The lesion involves the arm · the photograph is a close-up of the affected area · the subject is a female aged 30–39 — 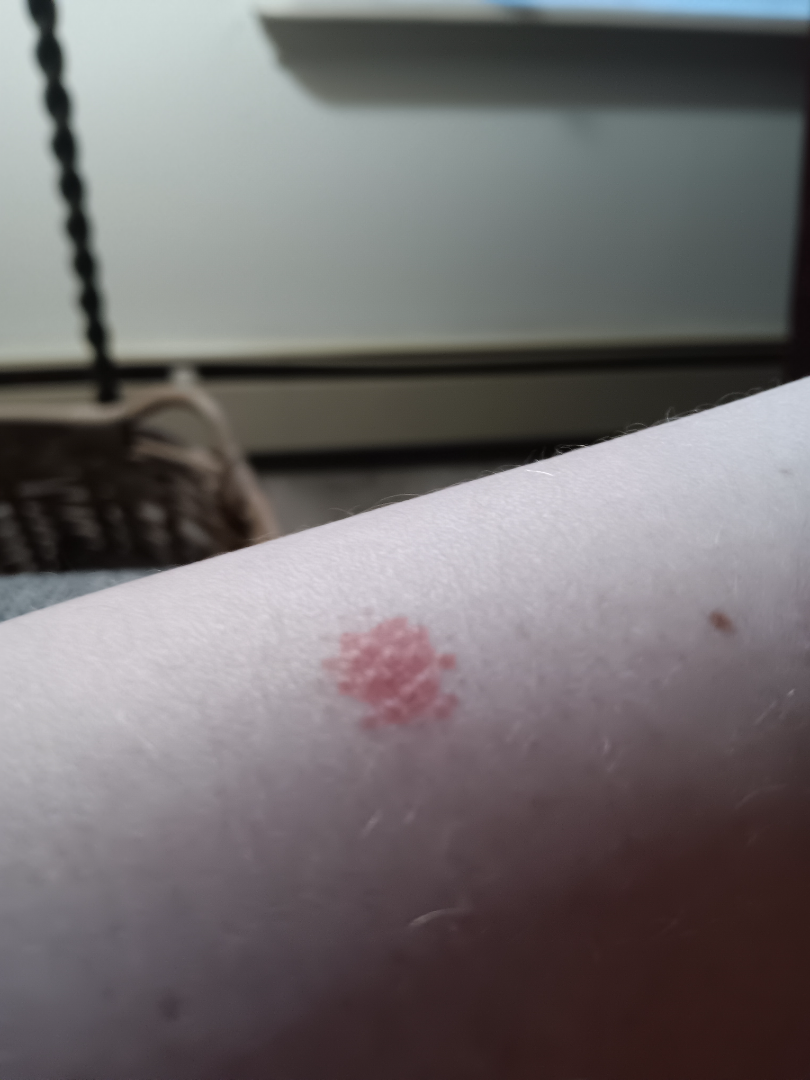<report>
<systemic_symptoms>shortness of breath, joint pain</systemic_symptoms>
<symptoms>bothersome appearance, itching</symptoms>
<patient_category>a rash</patient_category>
<texture>raised or bumpy</texture>
<duration>one to four weeks</duration>
<differential>
  <tied_lead>Acute dermatitis, NOS; Acute and chronic dermatitis</tied_lead>
</differential>
</report>